A dermoscopic photograph of a skin lesion:
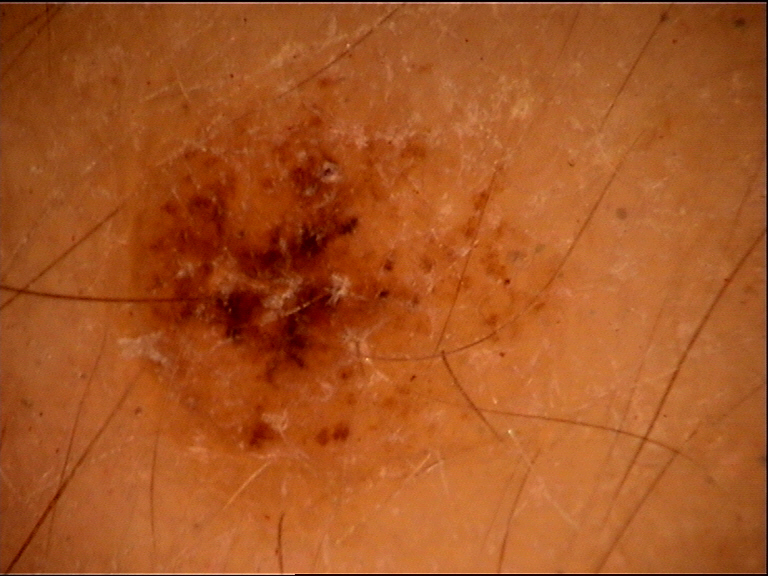The diagnostic label was a dysplastic compound nevus.